The subject is female. The lesion involves the leg. This image was taken at a distance: 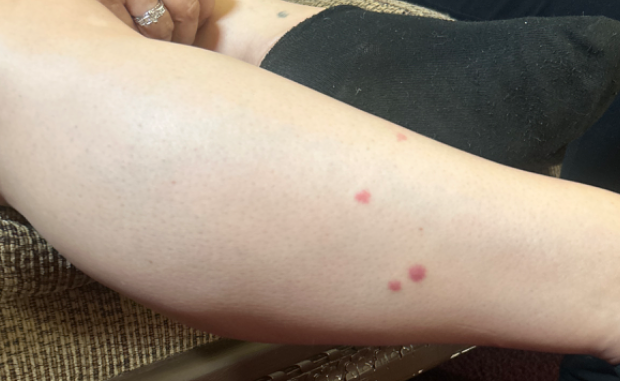skin tone: Fitzpatrick phototype III; lay reviewers estimated a MST of 2 | duration: less than one week | surface texture: raised or bumpy | clinical impression: the differential is split between Insect Bite and Leukocytoclastic Vasculitis.